A dermoscopic image of a skin lesion:
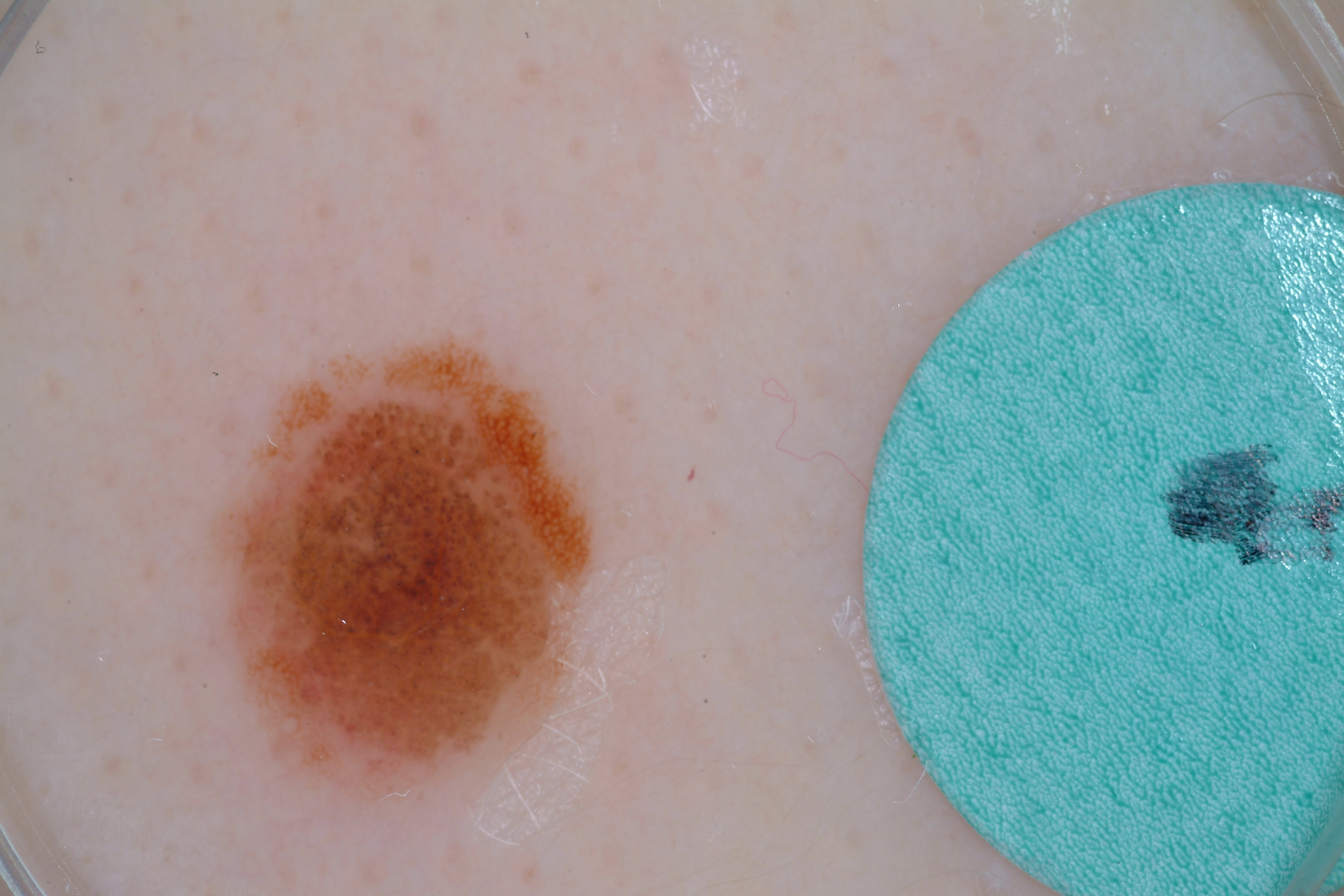With coordinates (x1, y1, x2, y2), the visible lesion spans [218, 345, 595, 792]. The lesion was assessed as a melanocytic nevus.